Close-up view · the lesion involves the leg · the condition has been present for less than one week · the lesion is associated with bothersome appearance, itching, burning and enlargement · the patient indicates the lesion is raised or bumpy.
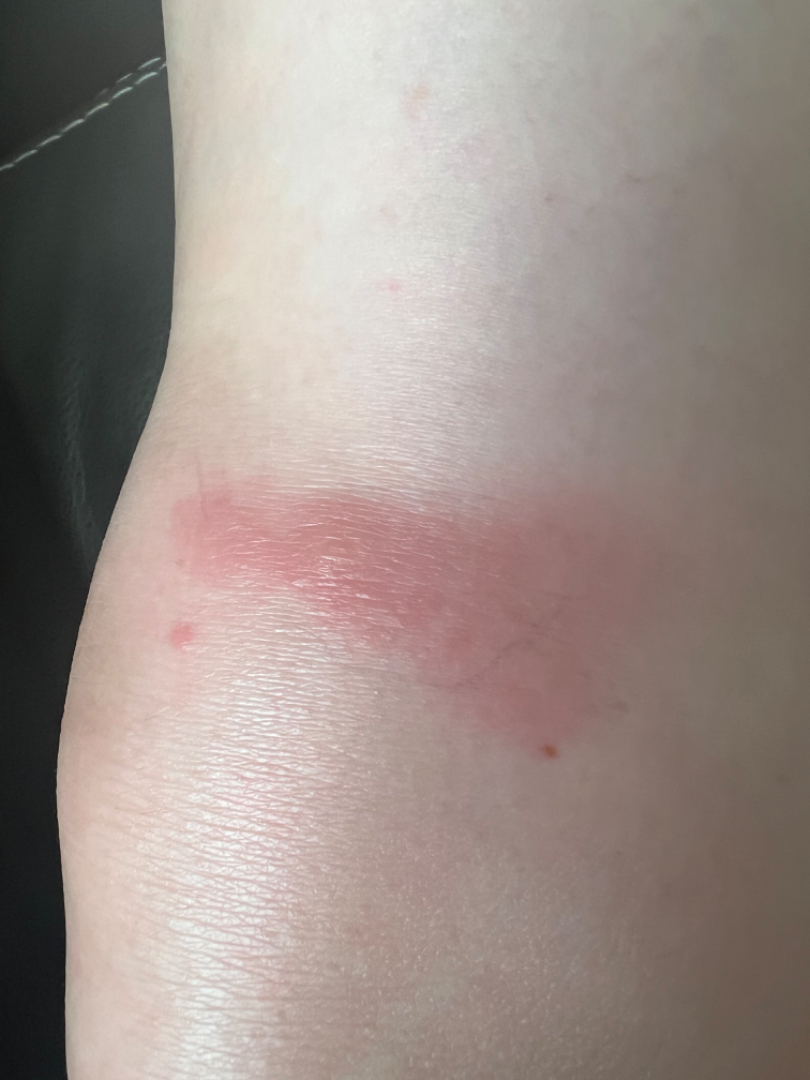assessment=not assessable.